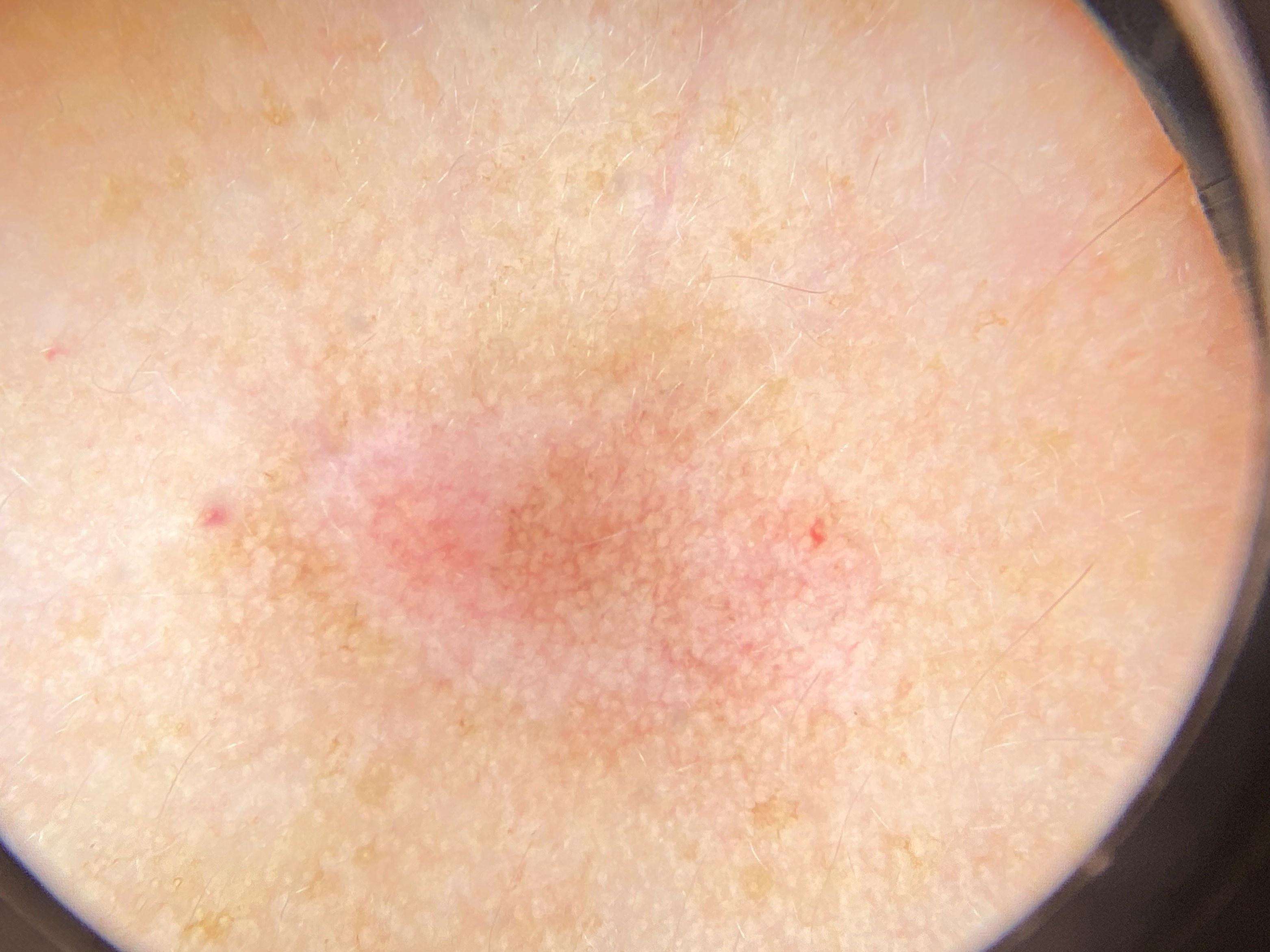{"diagnosis": {"name": "Solar or actinic keratosis", "malignancy": "indeterminate", "confirmation": "histopathology", "lineage": "epidermal"}}